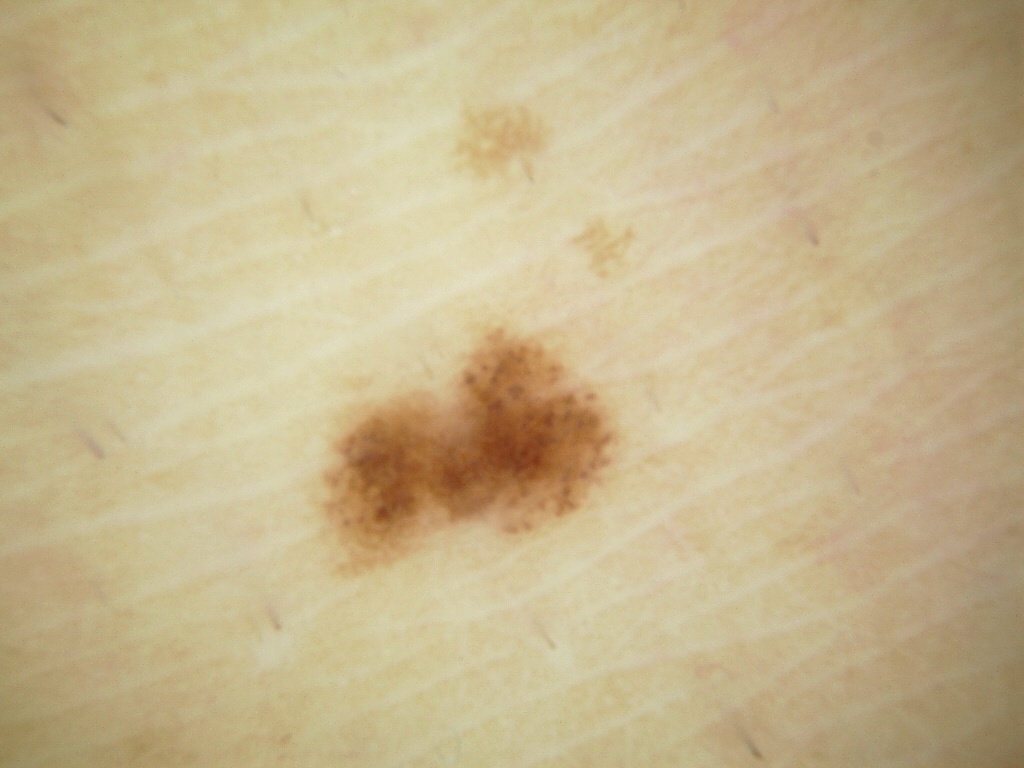image type: dermoscopy
lesion bbox: left=316, top=326, right=620, bottom=576
size: ~6% of the field
dermoscopic features not present: streaks and globules
assessment: a benign lesion